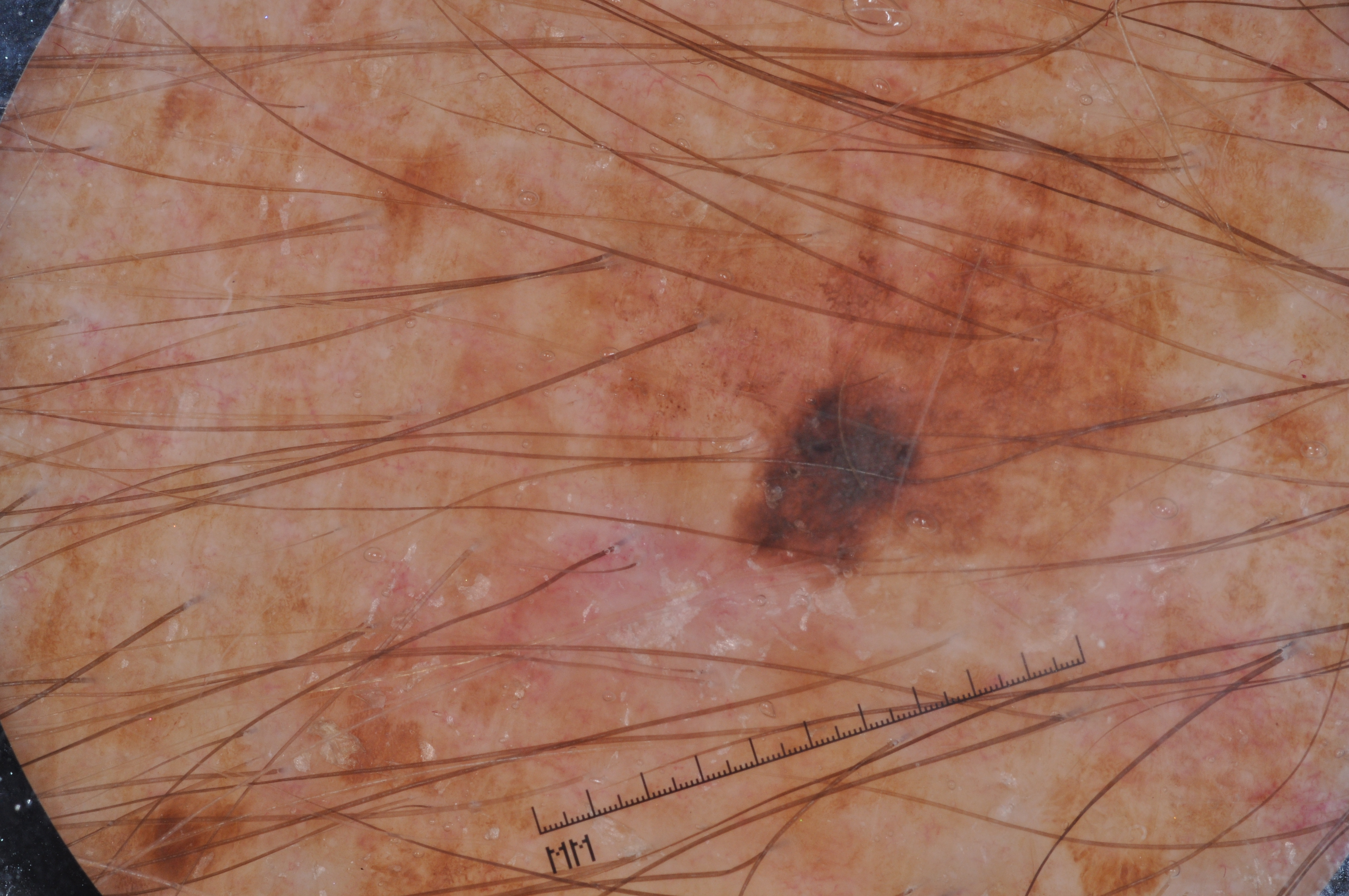The patient is a male aged approximately 70. A skin lesion imaged with a dermatoscope. On dermoscopy, the lesion shows pigment network. In (x1, y1, x2, y2) order, the lesion occupies the region [514,49,1267,607]. Biopsy-confirmed as a melanoma.